A dermoscopic photograph of a skin lesion:
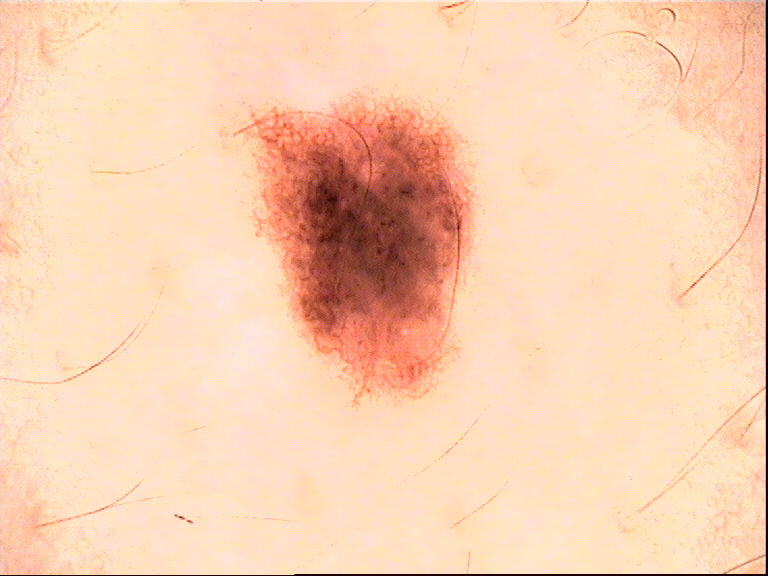| key | value |
|---|---|
| class | dysplastic compound nevus (expert consensus) |